A dermoscopic photograph of a skin lesion.
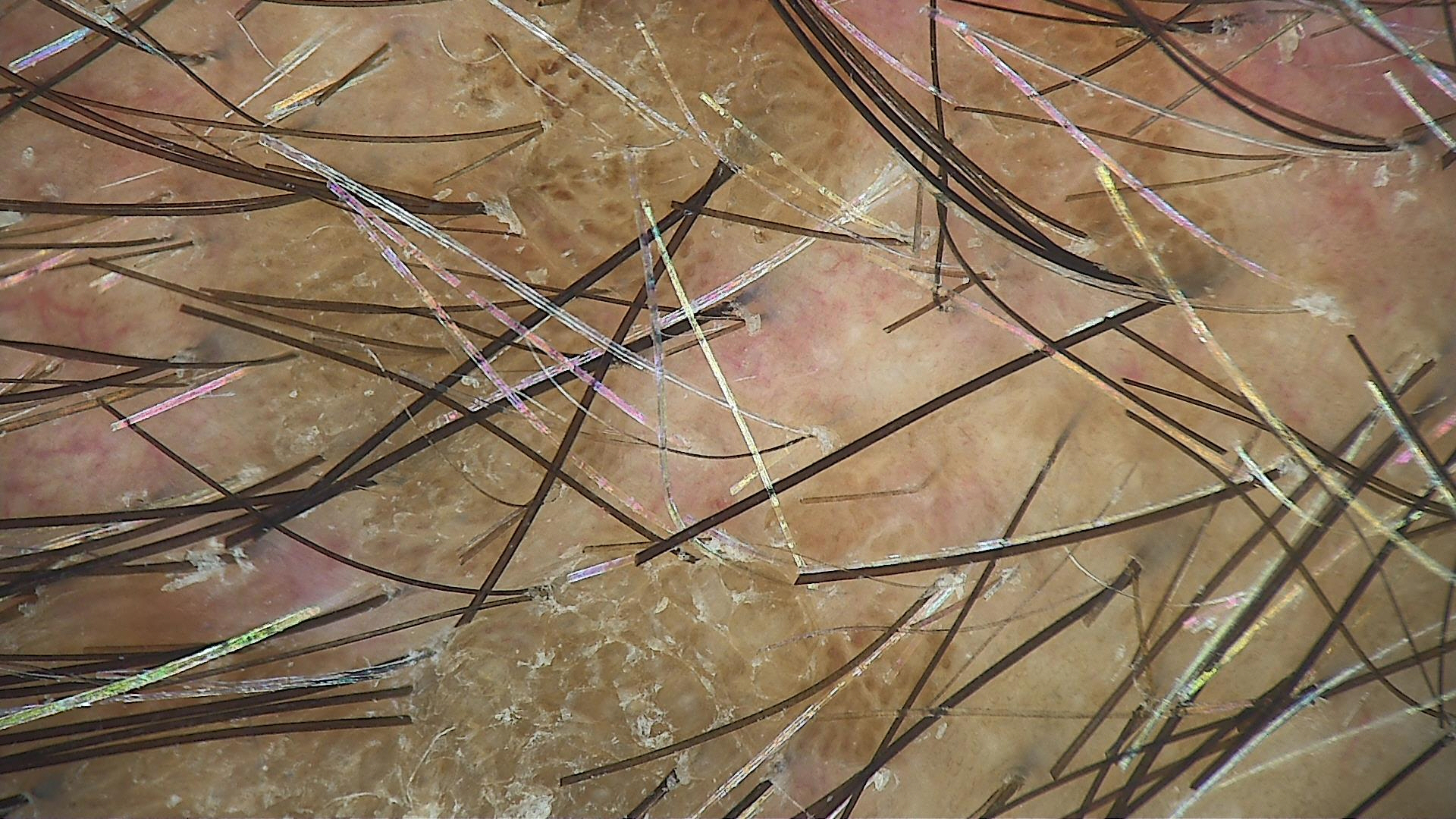The morphology is that of a keratinocytic lesion.
Consistent with a seborrheic keratosis.